A dermatoscopic image of a skin lesion:
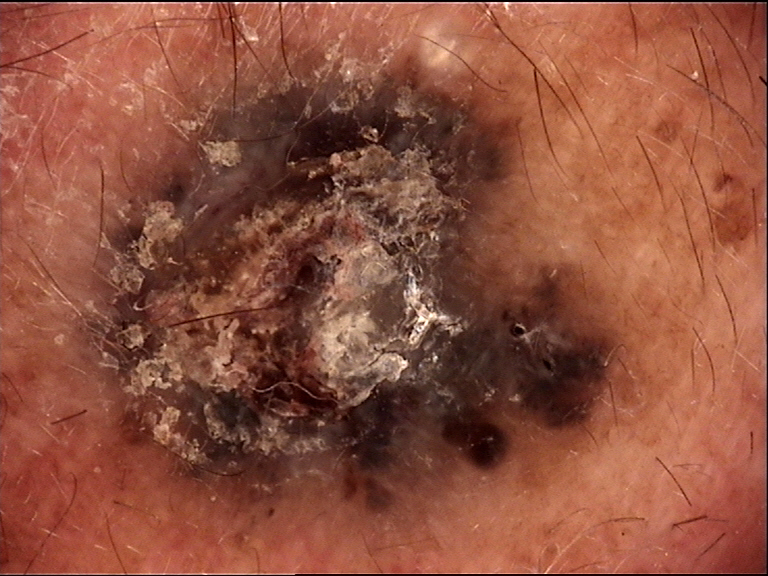| field | value |
|---|---|
| classification | keratinocytic |
| class | basal cell carcinoma (biopsy-proven) |